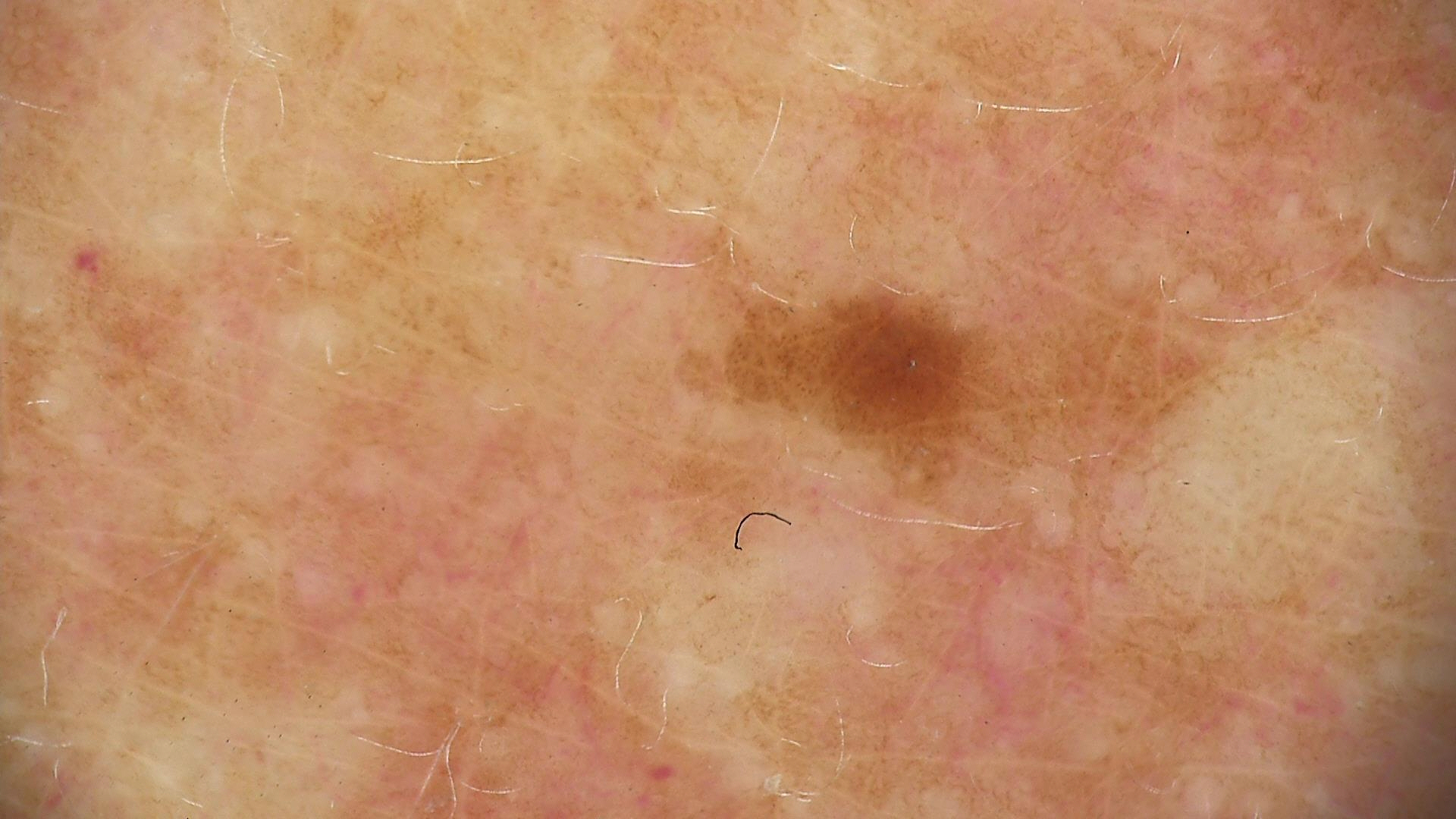Q: What is the imaging modality?
A: dermoscopy
Q: What is this lesion?
A: dysplastic junctional nevus (expert consensus)